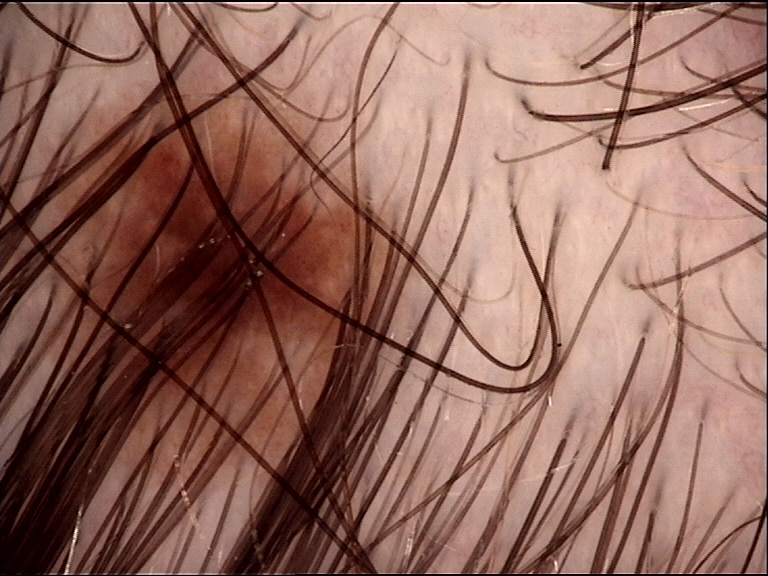image type: dermatoscopy
class: dysplastic junctional nevus (expert consensus)